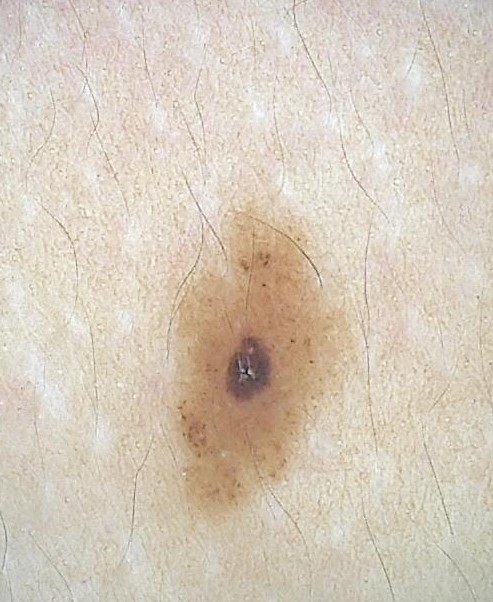diagnostic label=dysplastic compound nevus (expert consensus).